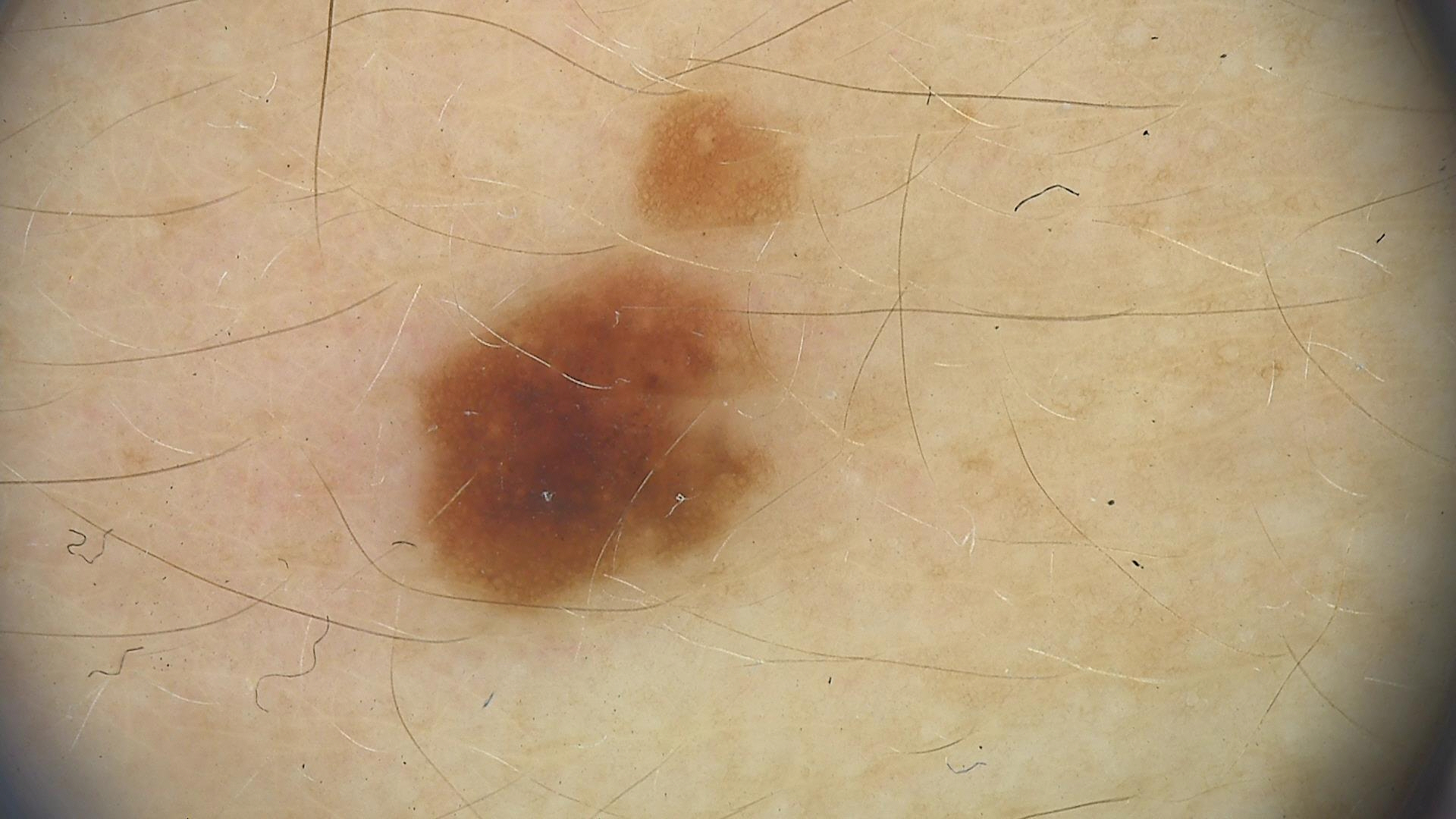Conclusion:
The diagnosis was a dysplastic junctional nevus.